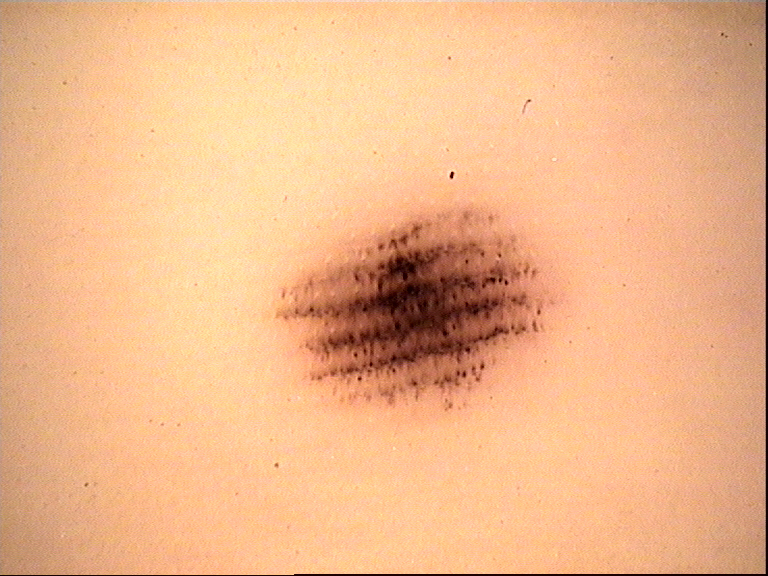Impression: The diagnostic label was an acral dysplastic junctional nevus.